This is a close-up image, the contributor notes itching, the contributor notes the condition has been present for about one day, lay reviewers estimated Monk Skin Tone 2, the affected area is the arm, texture is reported as raised or bumpy.
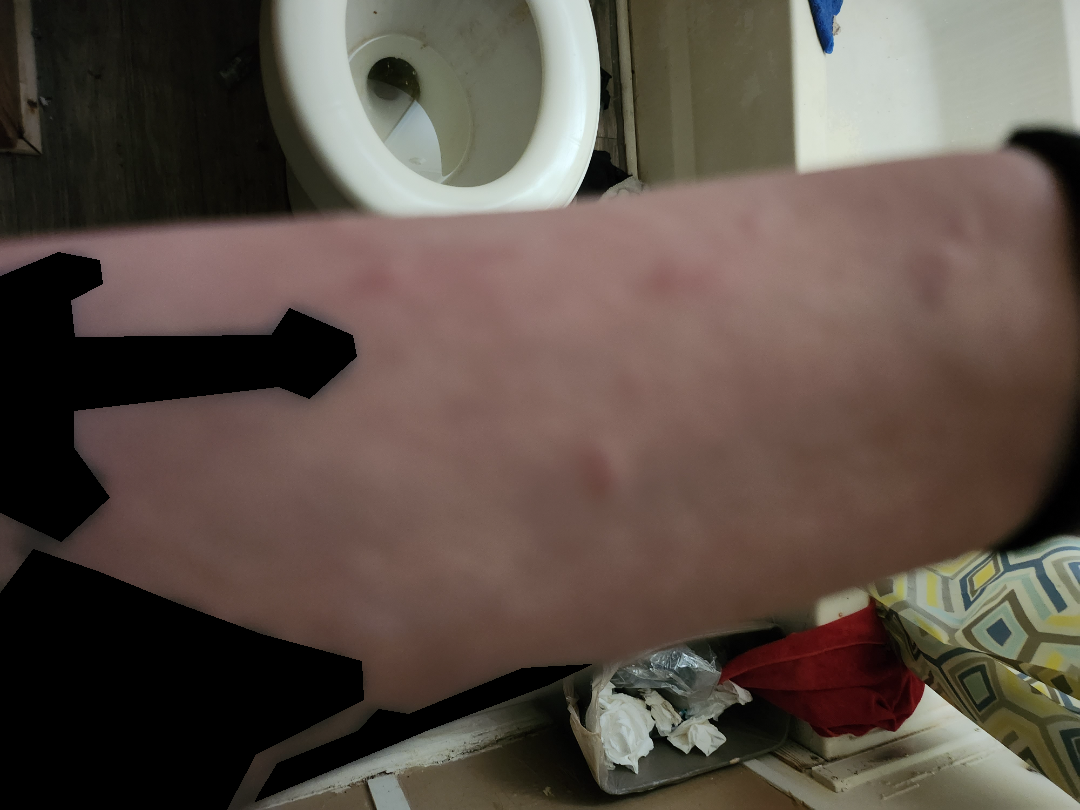The reviewing dermatologist was unable to assign a differential diagnosis from the image.